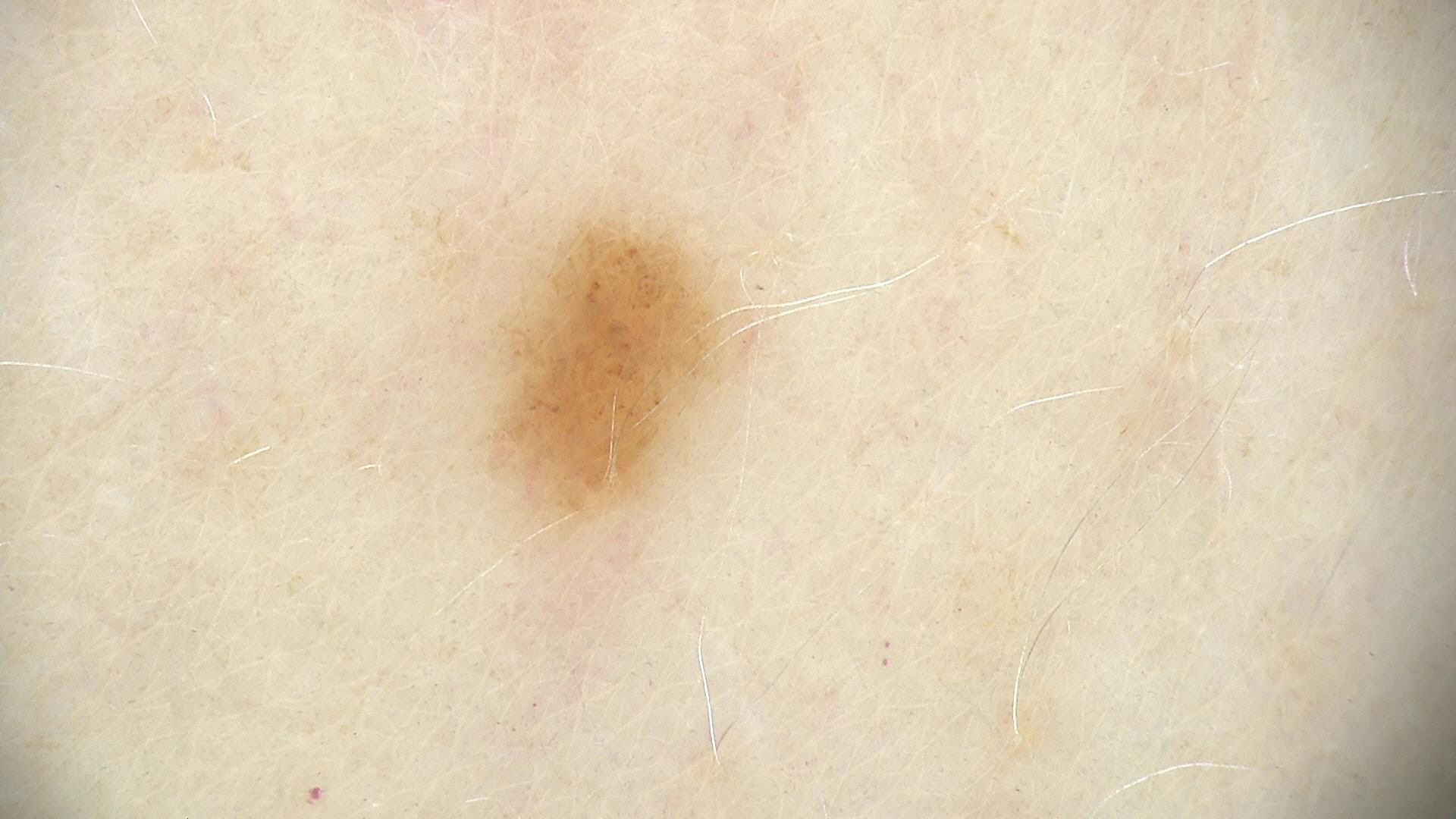<case>
<image>dermatoscopy</image>
<diagnosis>
<name>dysplastic junctional nevus</name>
<code>jd</code>
<malignancy>benign</malignancy>
<super_class>melanocytic</super_class>
<confirmation>expert consensus</confirmation>
</diagnosis>
</case>